The photograph was taken at a distance. Texture is reported as fluid-filled and raised or bumpy. The patient is a female aged 50–59. The patient notes burning, itching and bothersome appearance. Self-categorized by the patient as a rash: 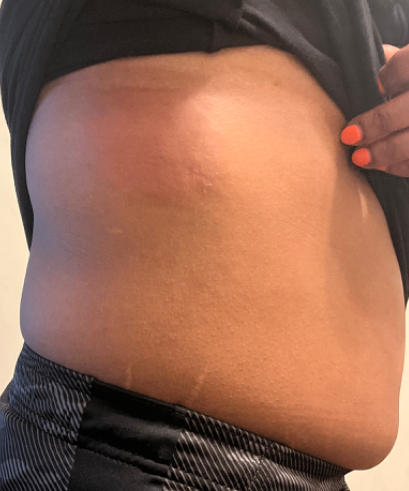| field | value |
|---|---|
| differential diagnosis | Urticaria and Erythema migrans were considered with similar weight; a more distant consideration is Allergic Contact Dermatitis |